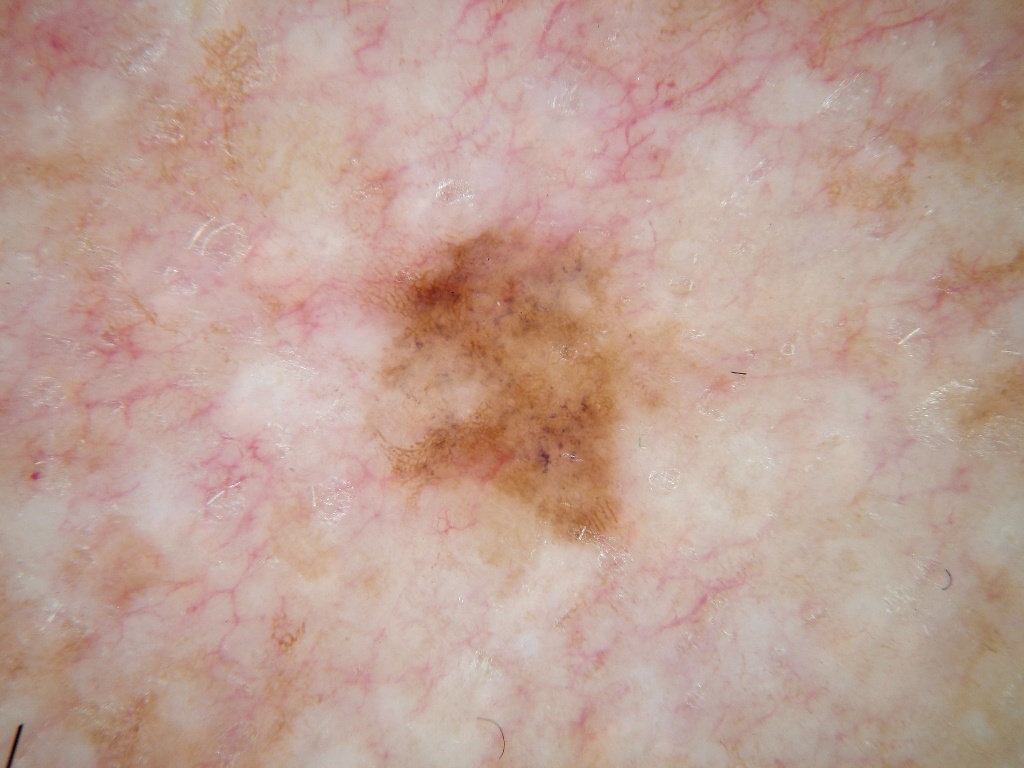This is a dermoscopic photograph of a skin lesion.
The lesion is bounded by <box>351, 216, 729, 563</box>.
The lesion occupies roughly 10% of the field.
Dermoscopically, the lesion shows pigment network.
Biopsy-confirmed as a melanoma.